A clinical photograph of a skin lesion. A patient in their 80s.
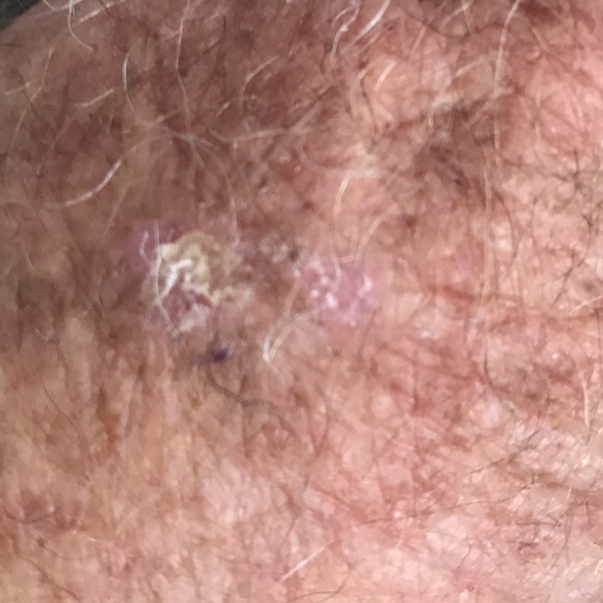location = a hand; reported symptoms = elevation, itching / no change in appearance; diagnostic label = actinic keratosis (clinical consensus).